An image taken at a distance · the back of the torso is involved · the patient reports the condition has been present for less than one week · skin tone: Fitzpatrick II · self-categorized by the patient as a rash · the patient reports burning, itching and pain · the patient is female · the patient reports the lesion is raised or bumpy, fluid-filled and rough or flaky.
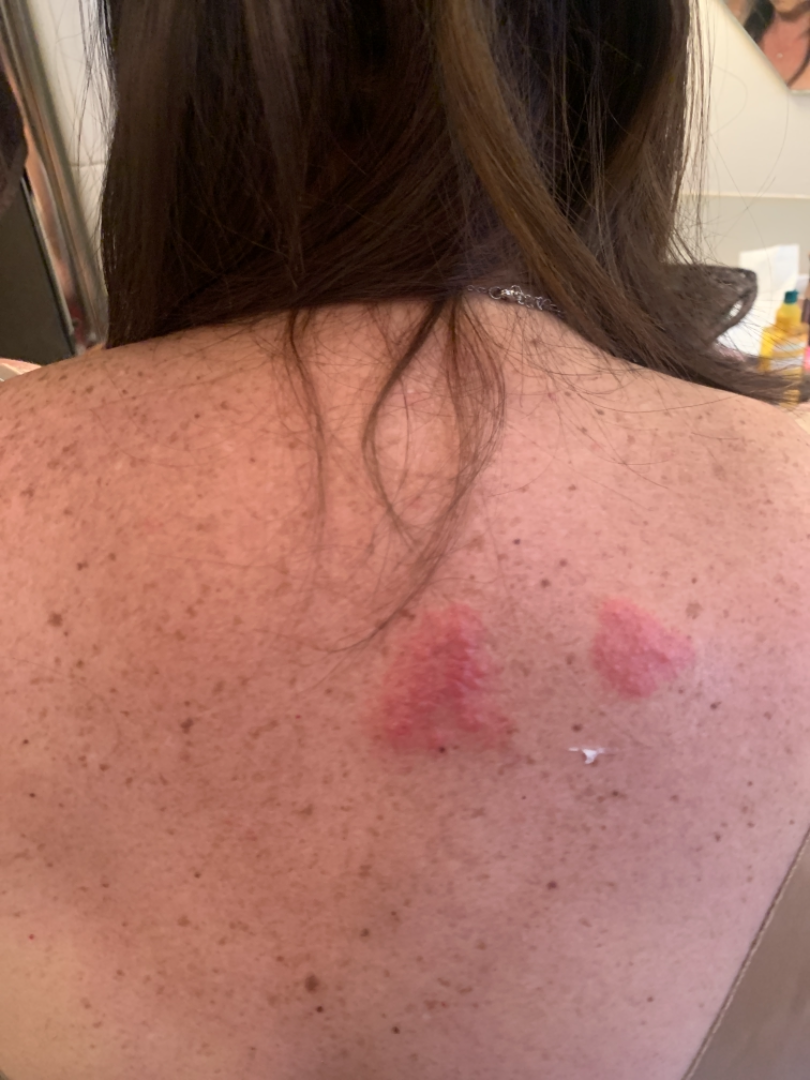- assessment · Herpes Zoster (0.58); Contact dermatitis (0.25); Allergic Contact Dermatitis (0.17)